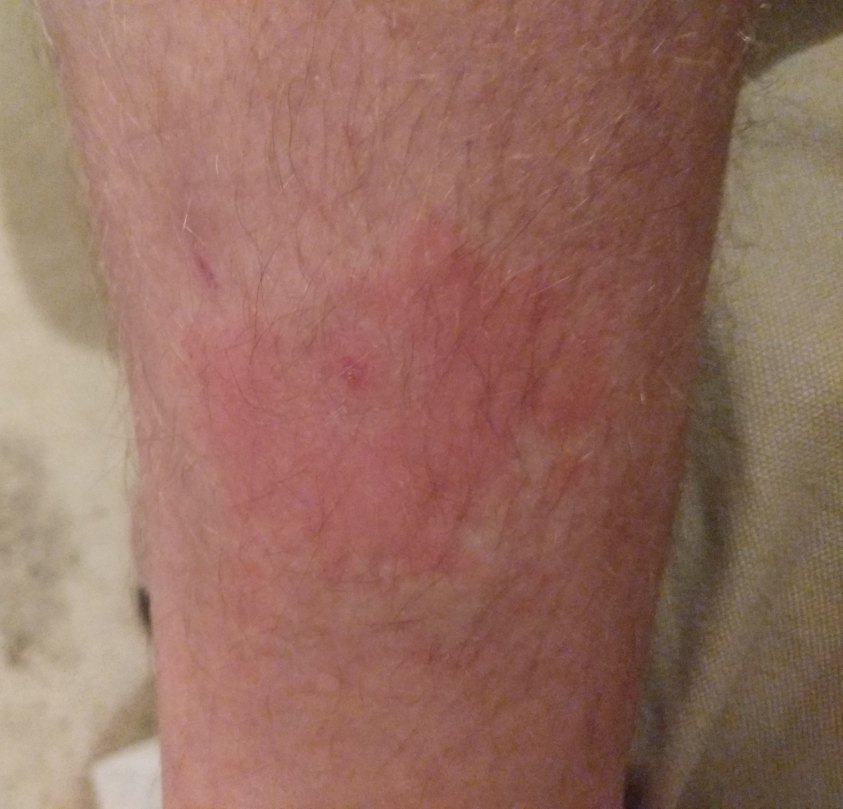diagnostic considerations = Insect Bite (0.54); Localized skin infection (0.23); Allergic Contact Dermatitis (0.23)